The arm is involved. The photograph is a close-up of the affected area:
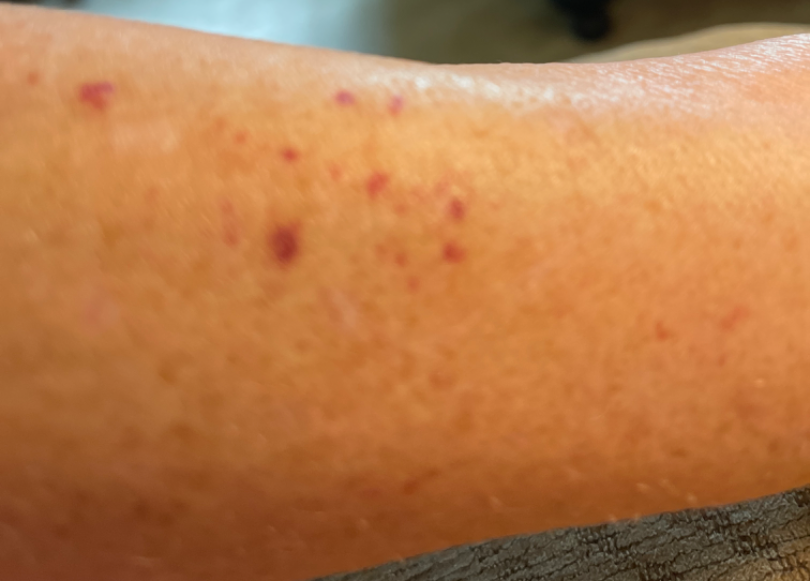The reviewing dermatologist was unable to assign a differential diagnosis from the image.